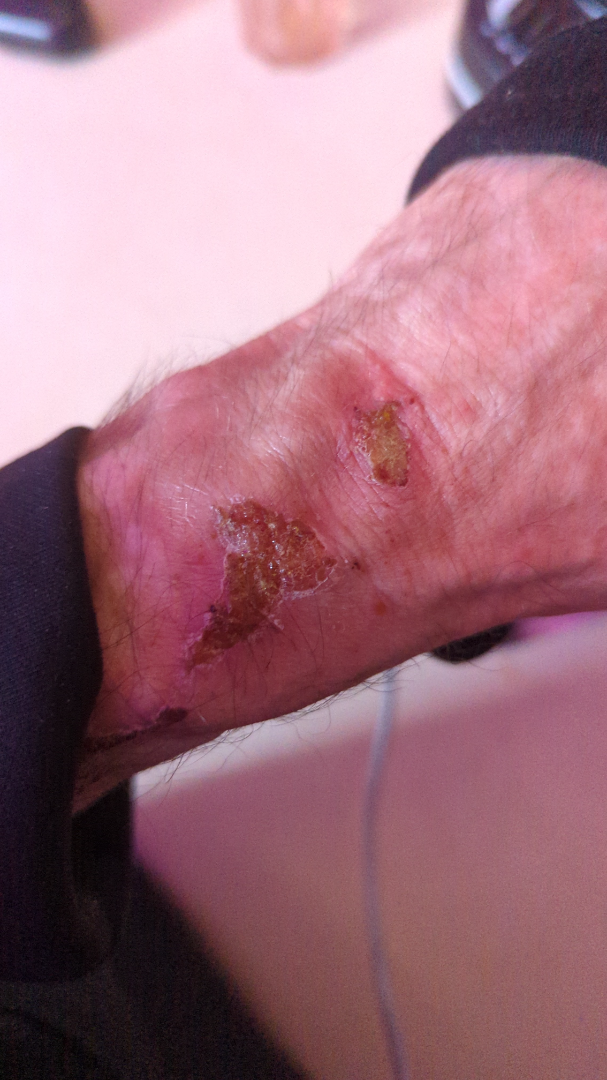  shot_type: close-up
  differential:
    leading:
      - Impetigo
    considered:
      - Bullous Pemphigoid